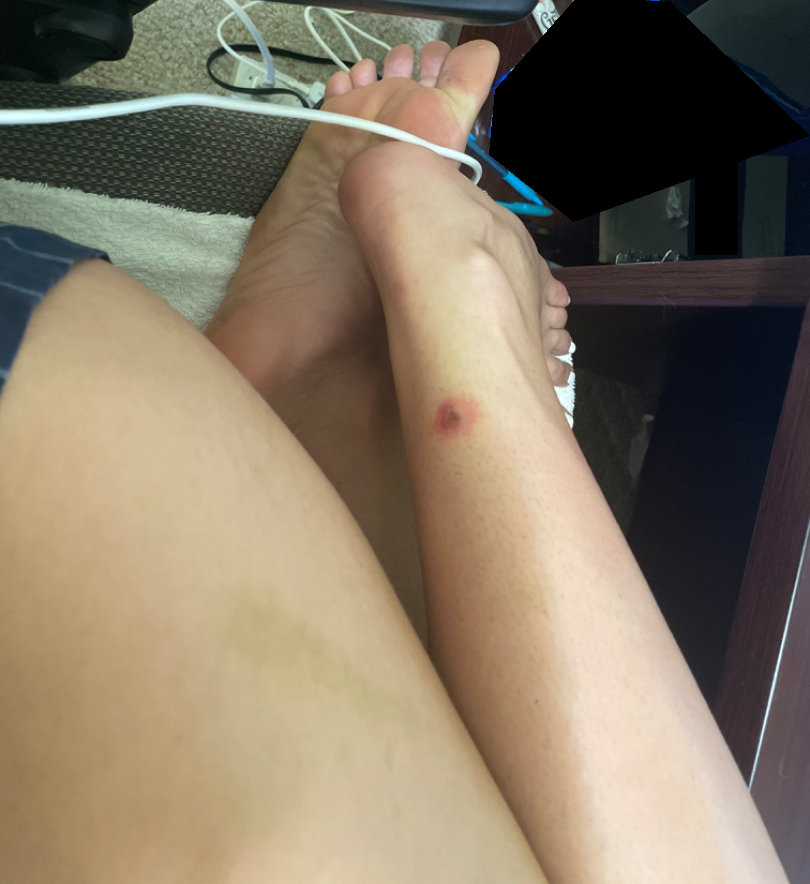The reviewing dermatologist was unable to assign a differential diagnosis from the image.
The photo was captured at a distance.